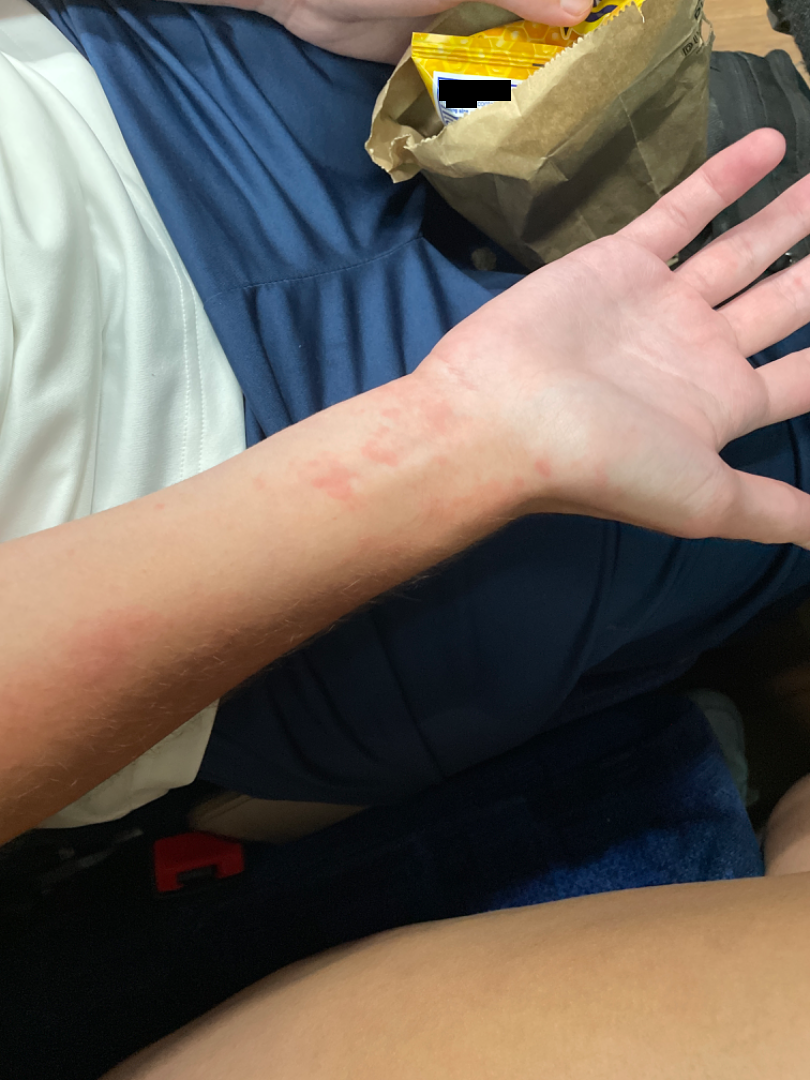The patient described the issue as a rash. The lesion involves the arm and back of the hand. Reported lesion symptoms include itching. The photo was captured at a distance. The condition has been present for less than one week. The patient reports the lesion is raised or bumpy. On dermatologist assessment of the image, Eczema, Allergic Contact Dermatitis and Irritant Contact Dermatitis were considered with similar weight.